A dermatoscopic image of a skin lesion:
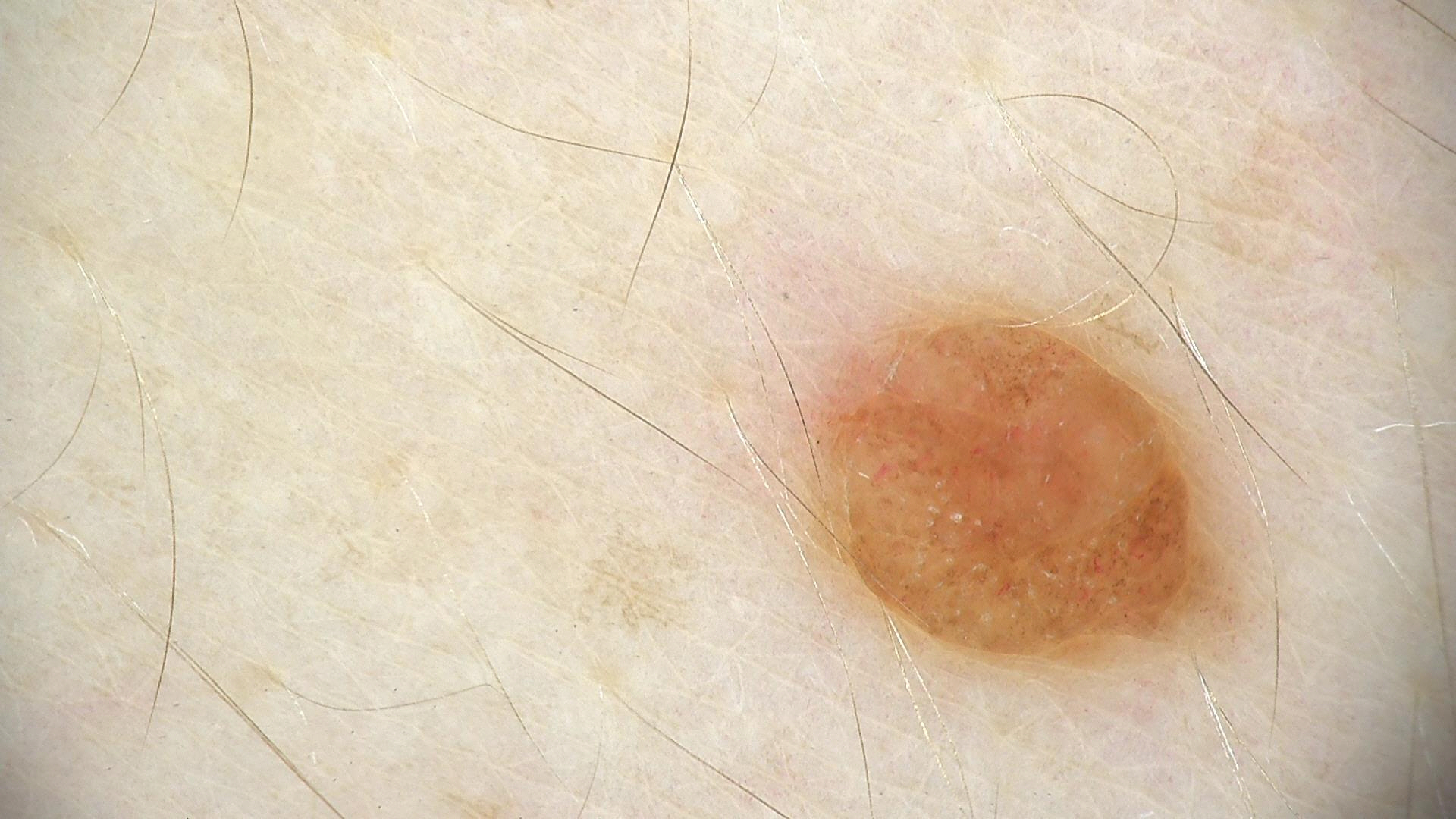This is a banal lesion. Consistent with a compound nevus.